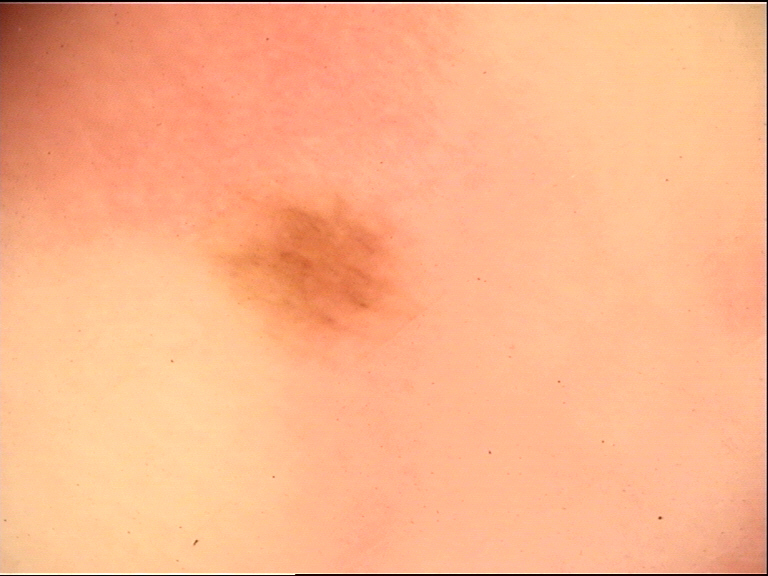A dermoscopy image of a single skin lesion. The architecture is that of a banal lesion. Classified as an acral junctional nevus.